A dermoscopy image of a single skin lesion: 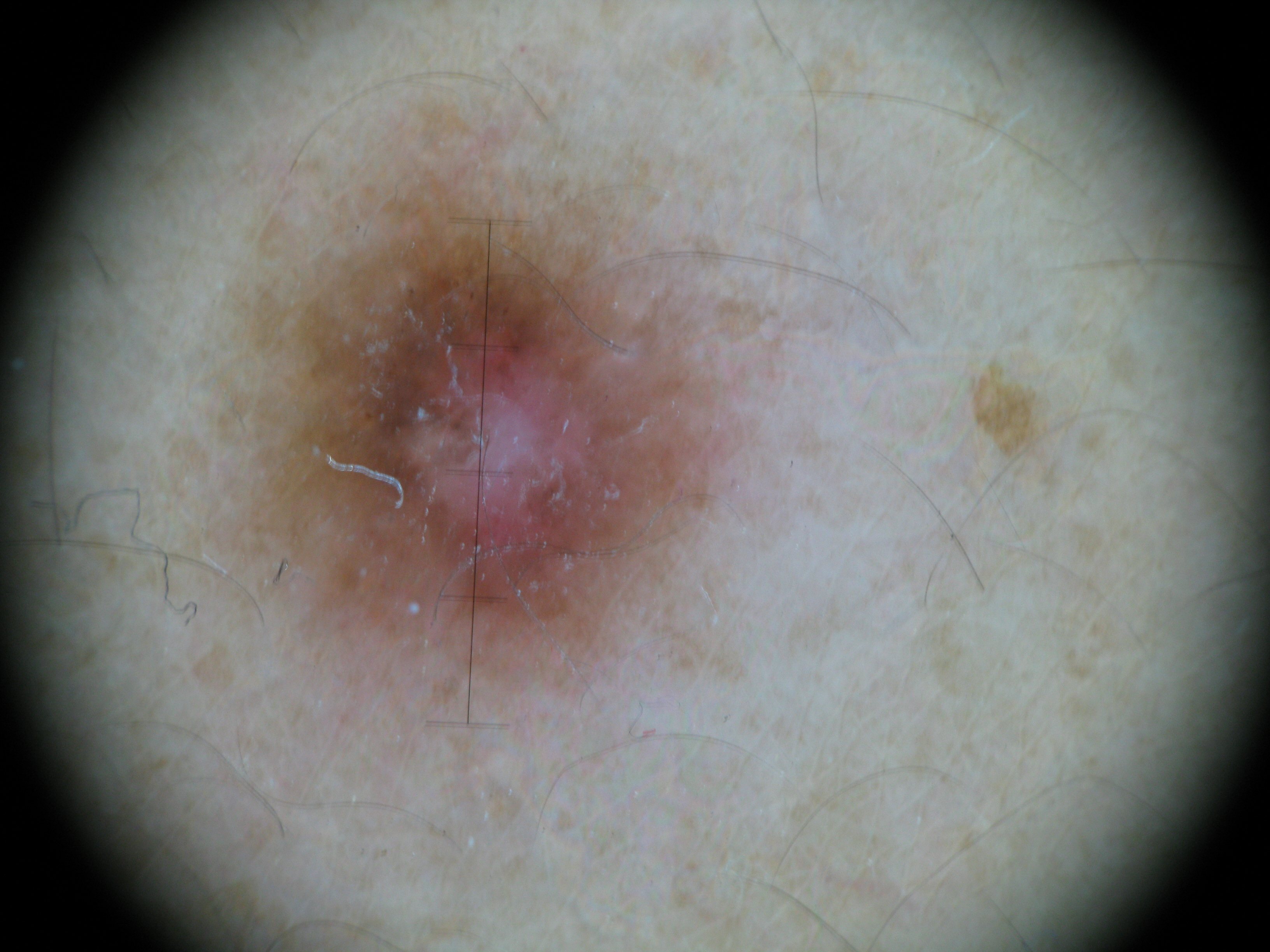subtype: fibro-histiocytic, class: dermatofibroma (expert consensus).